The contributor notes the lesion is raised or bumpy · this is a close-up image · FST I; lay graders estimated MST 1 or 3 (two reviewer pools disagreed) · the lesion involves the front of the torso and leg · the contributor notes itching · reported duration is less than one week — 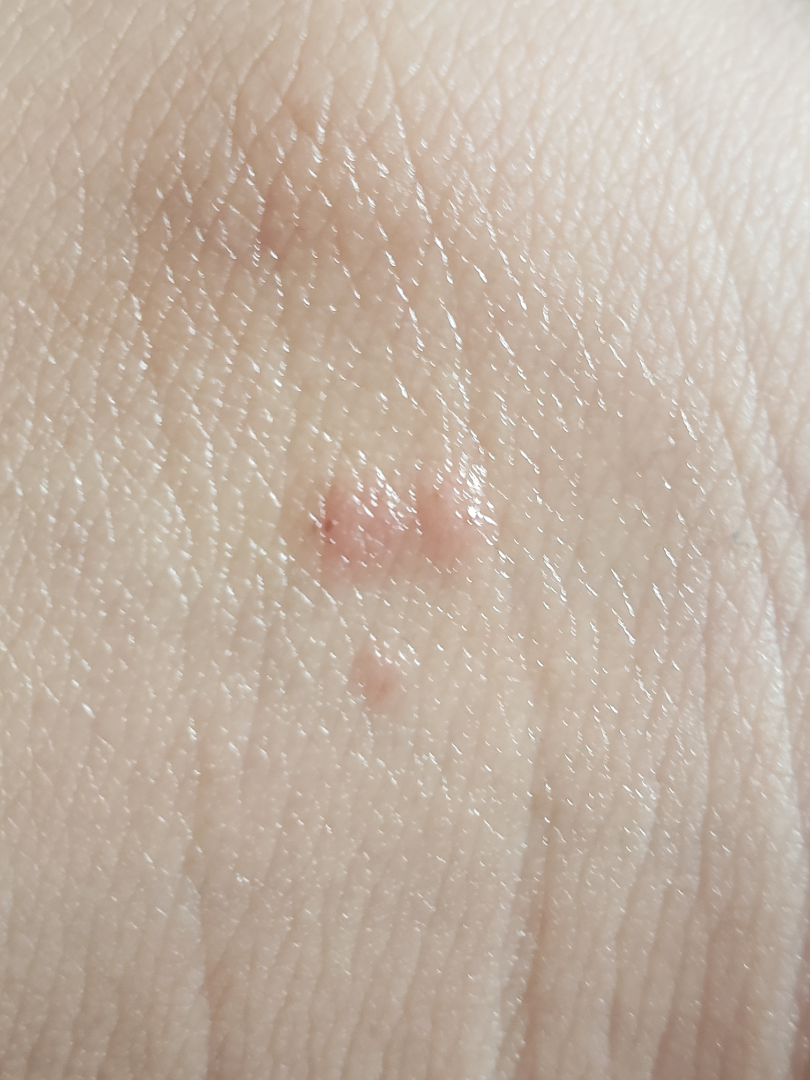<dermatology_case>
<assessment>not assessable</assessment>
</dermatology_case>